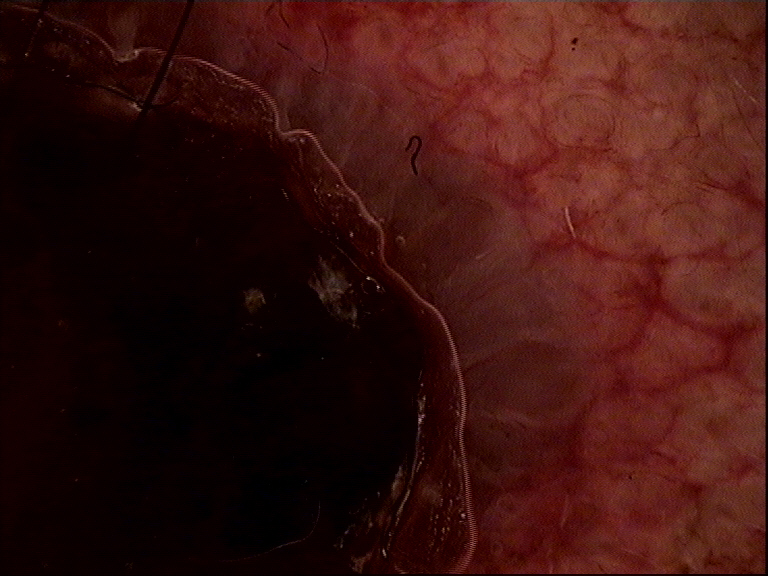<case>
  <diagnosis>
    <name>squamous cell carcinoma</name>
    <code>scc</code>
    <malignancy>malignant</malignancy>
    <super_class>non-melanocytic</super_class>
    <confirmation>histopathology</confirmation>
  </diagnosis>
</case>